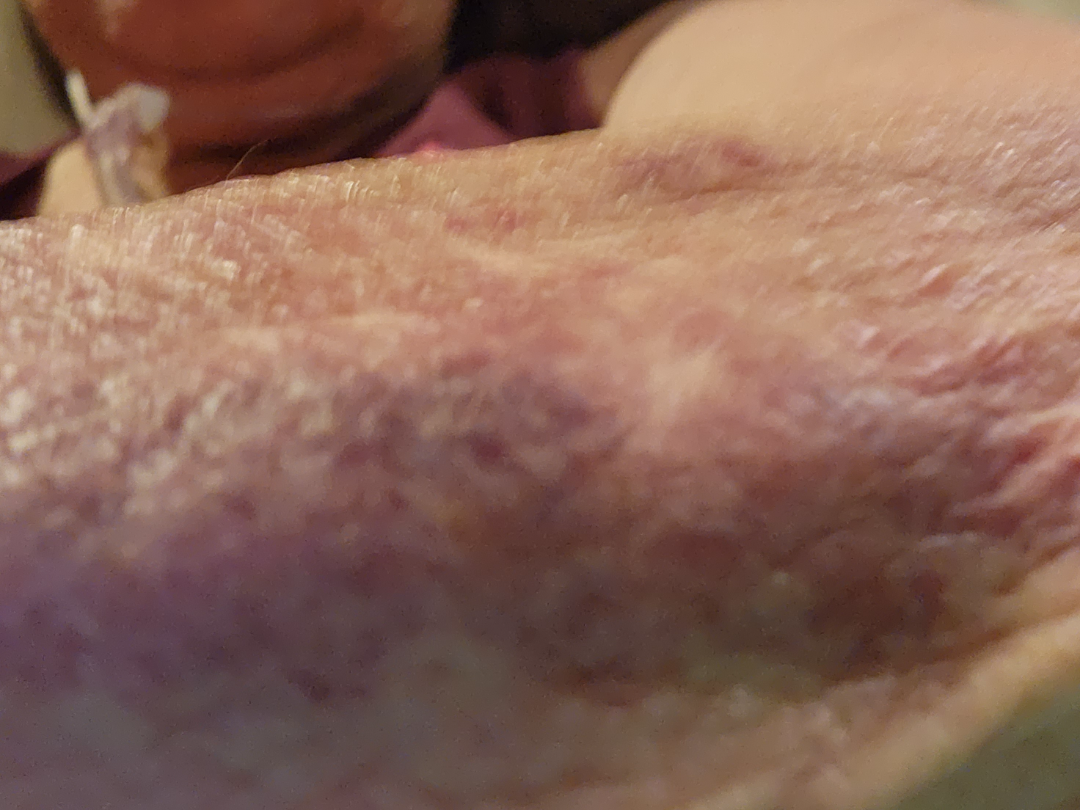Case summary:
* assessment — not assessable
* photo taken — close-up
* anatomic site — arm